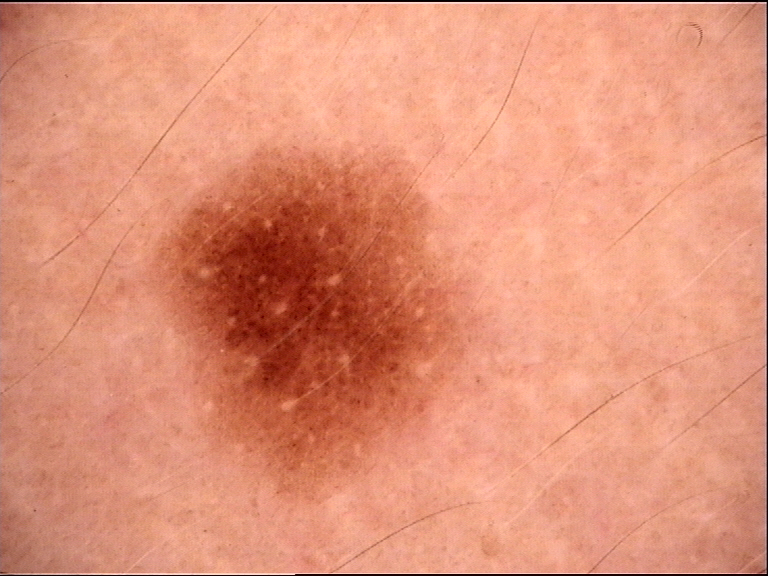Consistent with a banal lesion — a junctional nevus.